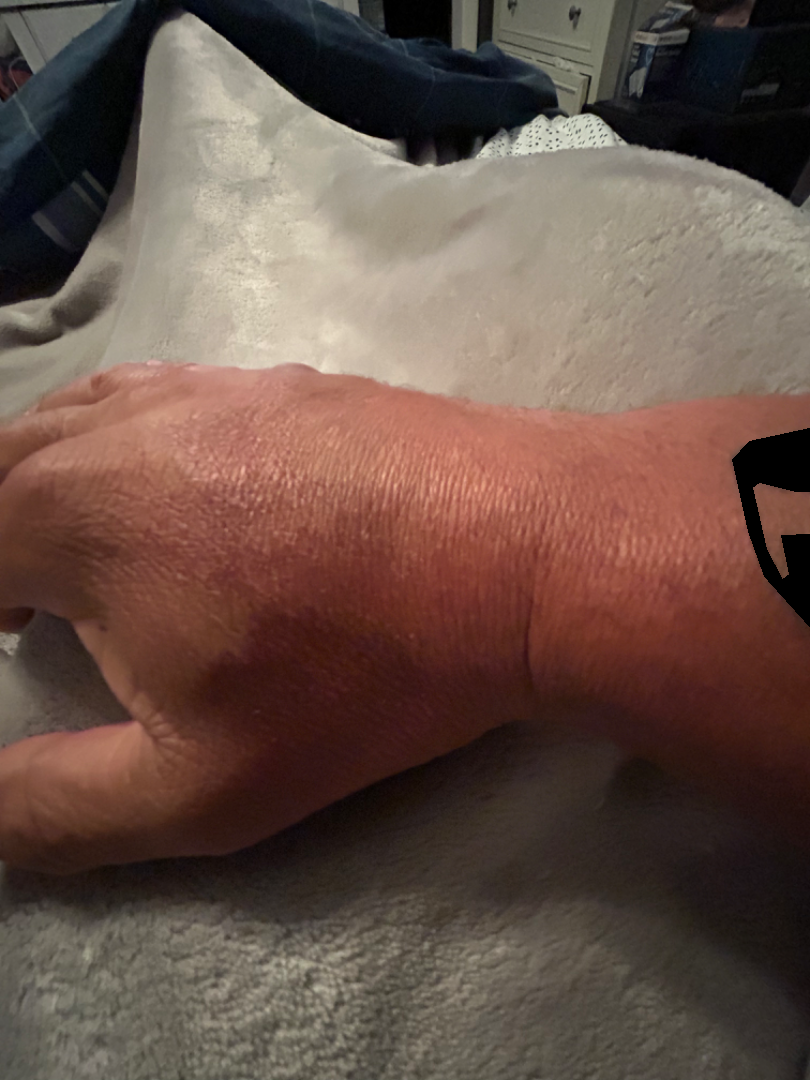A close-up photograph. On photographic review: the leading impression is Granuloma annulare; also raised was Tinea; an alternative is Eczema.